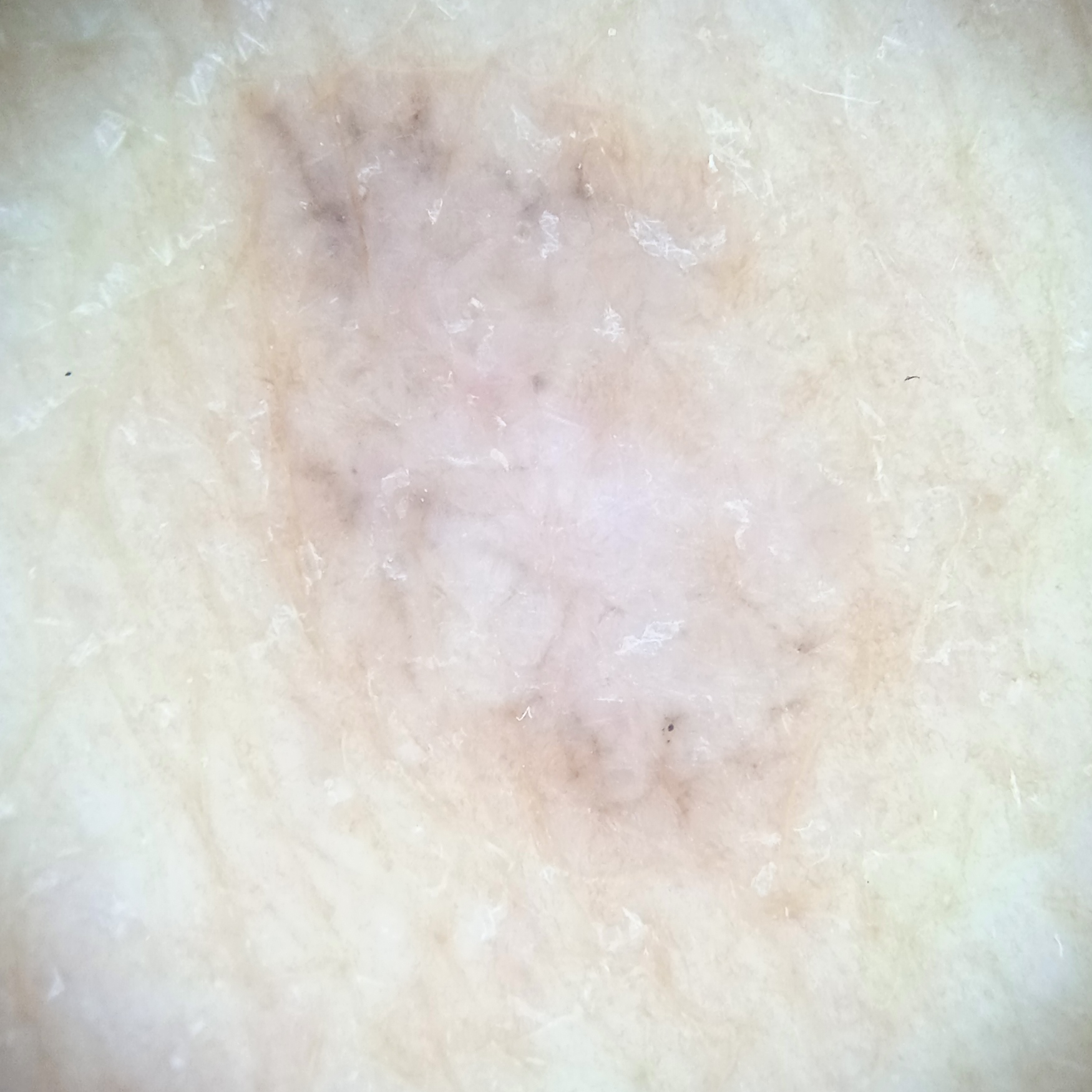The patient describes having few moles overall.
Acquired for a research image collection, with no referral diagnosis.
The patient says their skin tans without first burning.
The lesion measures approximately 10.4 mm.
The diagnostic impression was a basal cell carcinoma.